A dermoscopic close-up of a skin lesion.
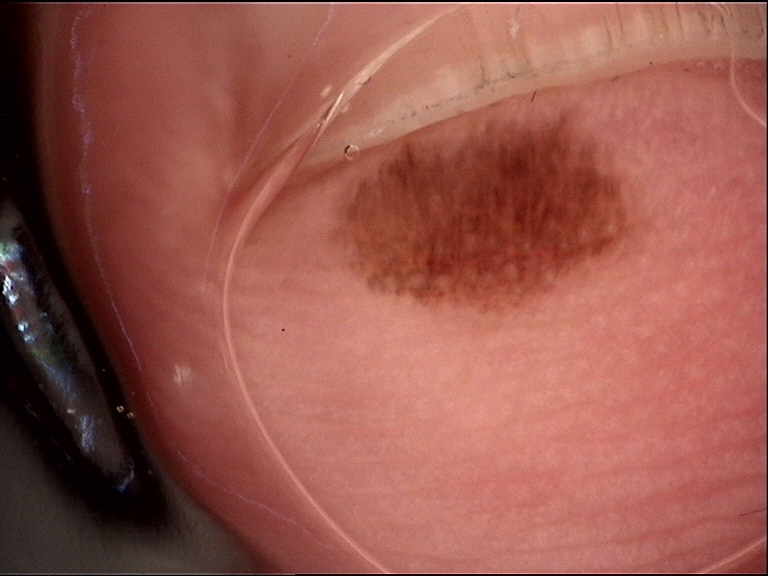diagnostic label = acral junctional nevus (expert consensus).